Dermoscopy of a skin lesion. By self-report, a personal history of skin cancer, immunosuppression, and a family history of skin cancer. The patient says their skin reddens painfully with sun exposure.
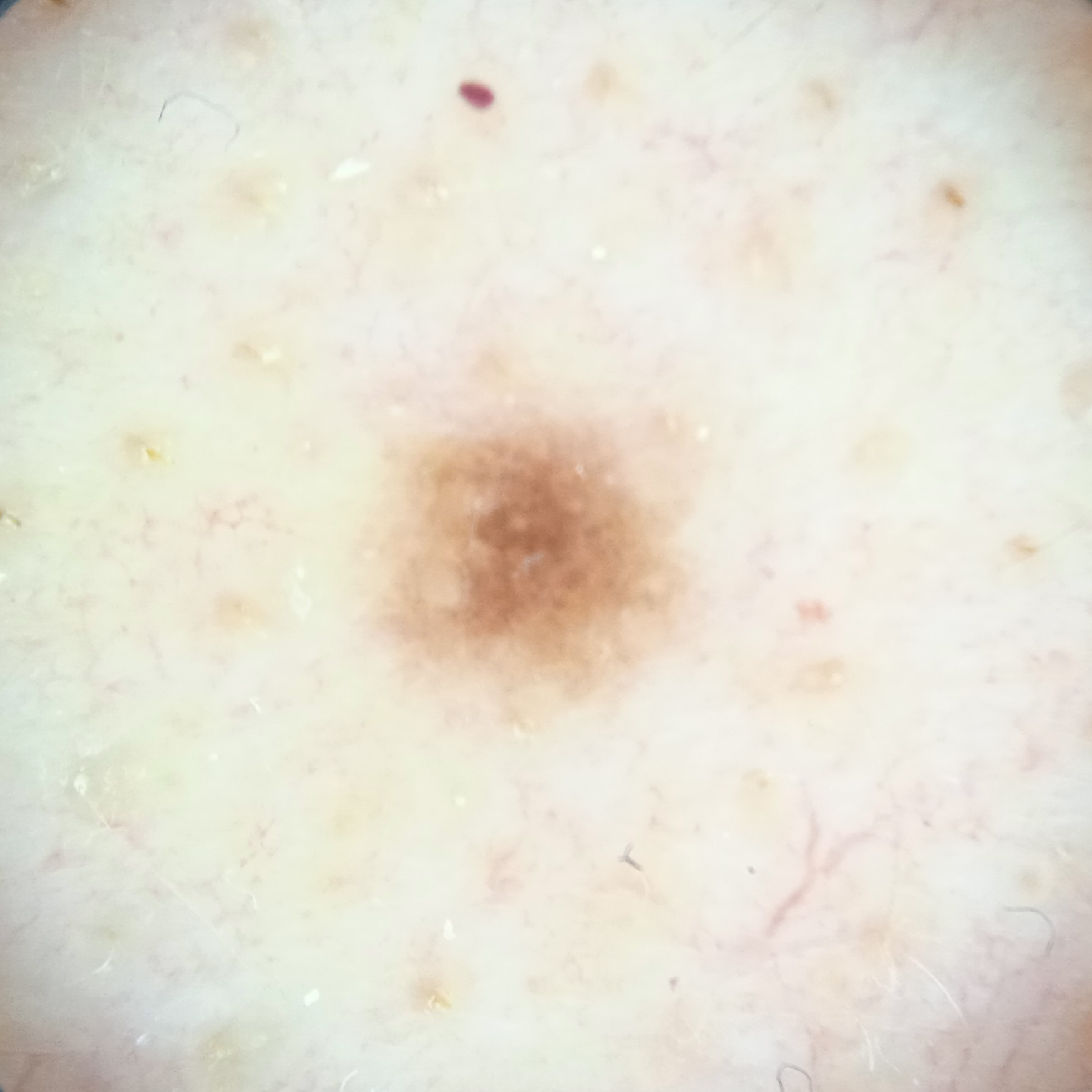Clinical context:
Measuring roughly 3.6 mm.
Conclusion:
The four-dermatologist consensus diagnosis was a melanocytic nevus; the reviewers were moderately confident; an alternative consideration was a seborrheic keratosis.